This image was taken at an angle. The front of the torso is involved. The contributor is 60–69, female — 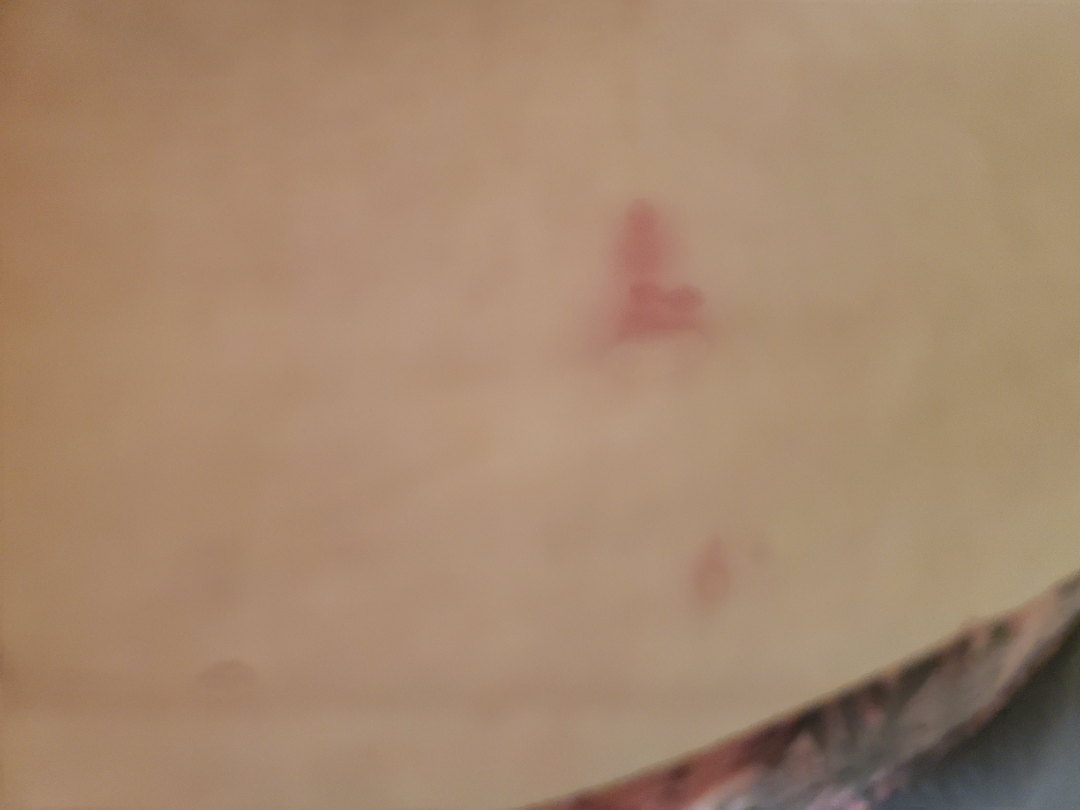The reviewer was unable to grade this case for skin condition.